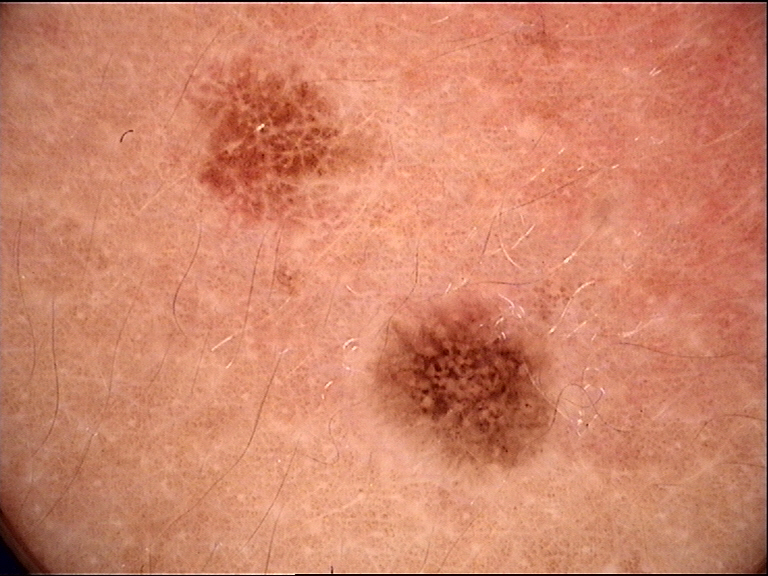Findings: A dermoscopy image of a single skin lesion. Impression: Consistent with a dysplastic junctional nevus.